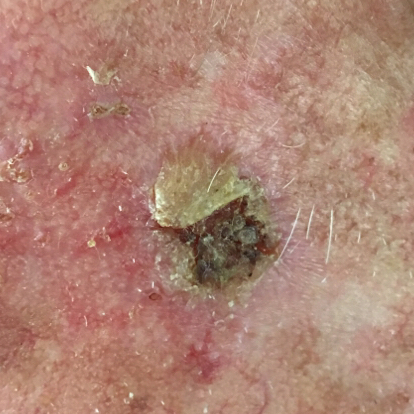subject=male, 66 years of age; location=an ear; lesion size=approx. 20 × 15 mm; symptoms=itching, bleeding, elevation, pain; pathology=actinic keratosis (biopsy-proven).